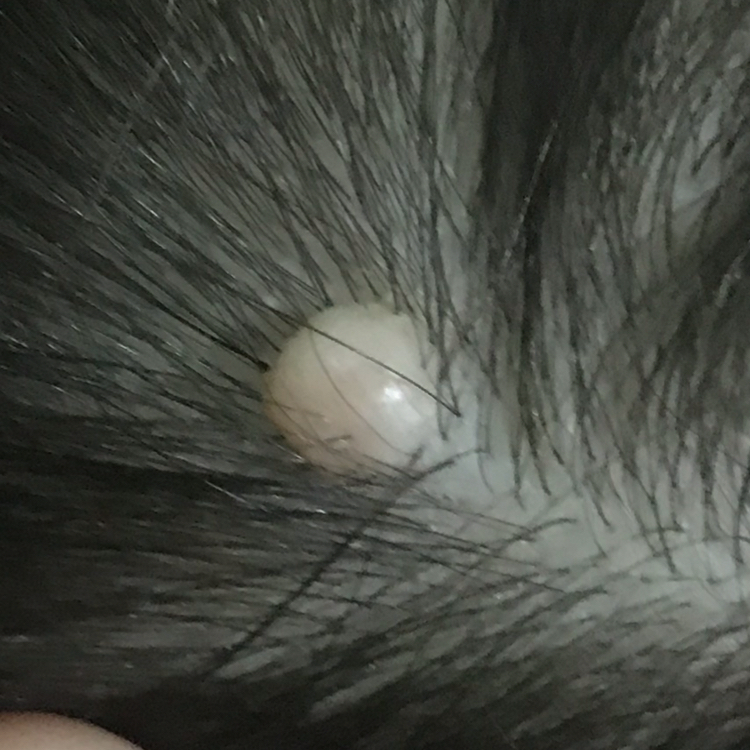Findings: A clinical photo of a skin lesion taken with a smartphone. A subject 31 years of age. The lesion was found on the scalp. The patient reports that the lesion has grown and is elevated, but does not itch and has not bled. Conclusion: The clinical impression was a nevus.